A close-up photograph · female subject, age 40–49 · the arm is involved:
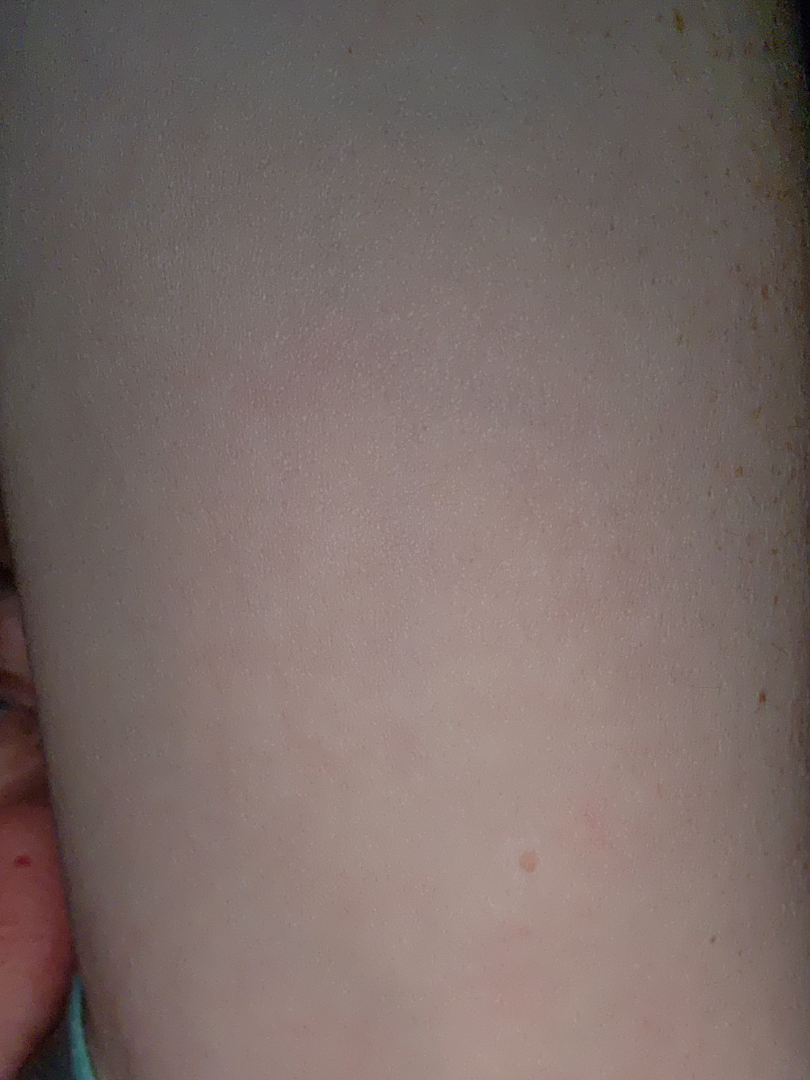Q: Could the case be diagnosed?
A: no clear pathology
Q: What is the lesion texture?
A: fluid-filled and raised or bumpy
Q: What symptoms does the patient report?
A: enlargement and pain
Q: Any systemic symptoms?
A: joint pain, fatigue and chills